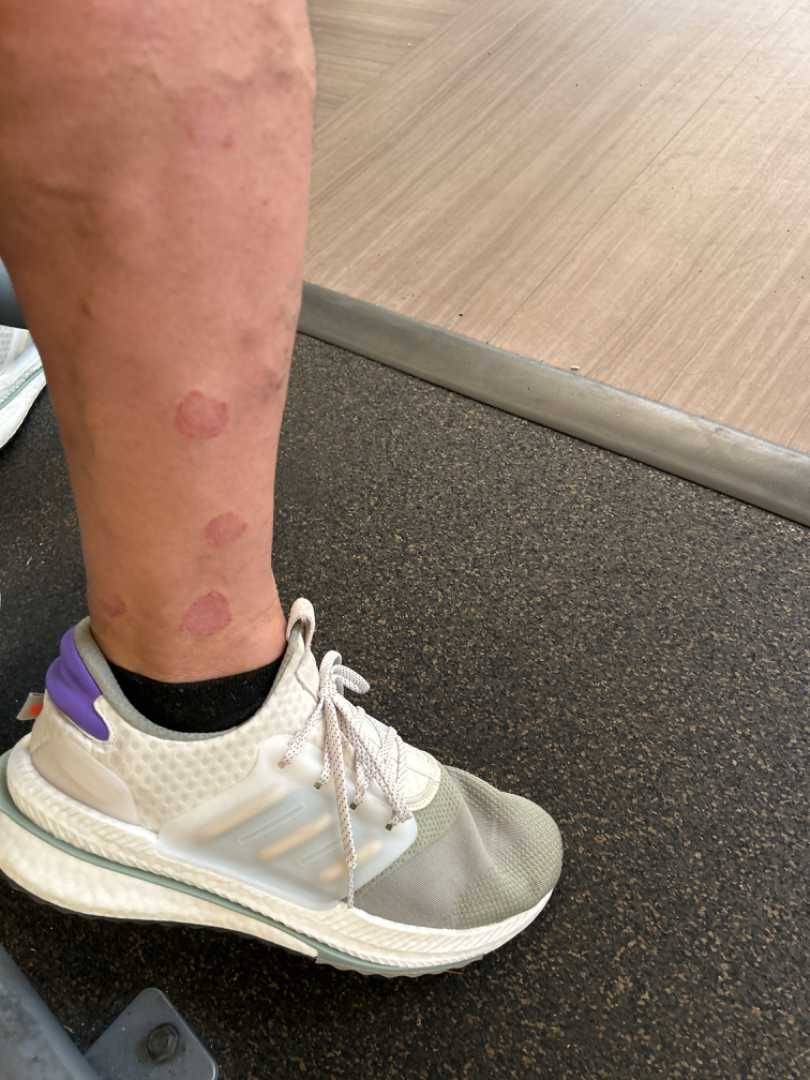• location: leg
• framing: at a distance
• impression: most consistent with Eczema; the differential also includes Parapsoriasis; with consideration of Psoriasis